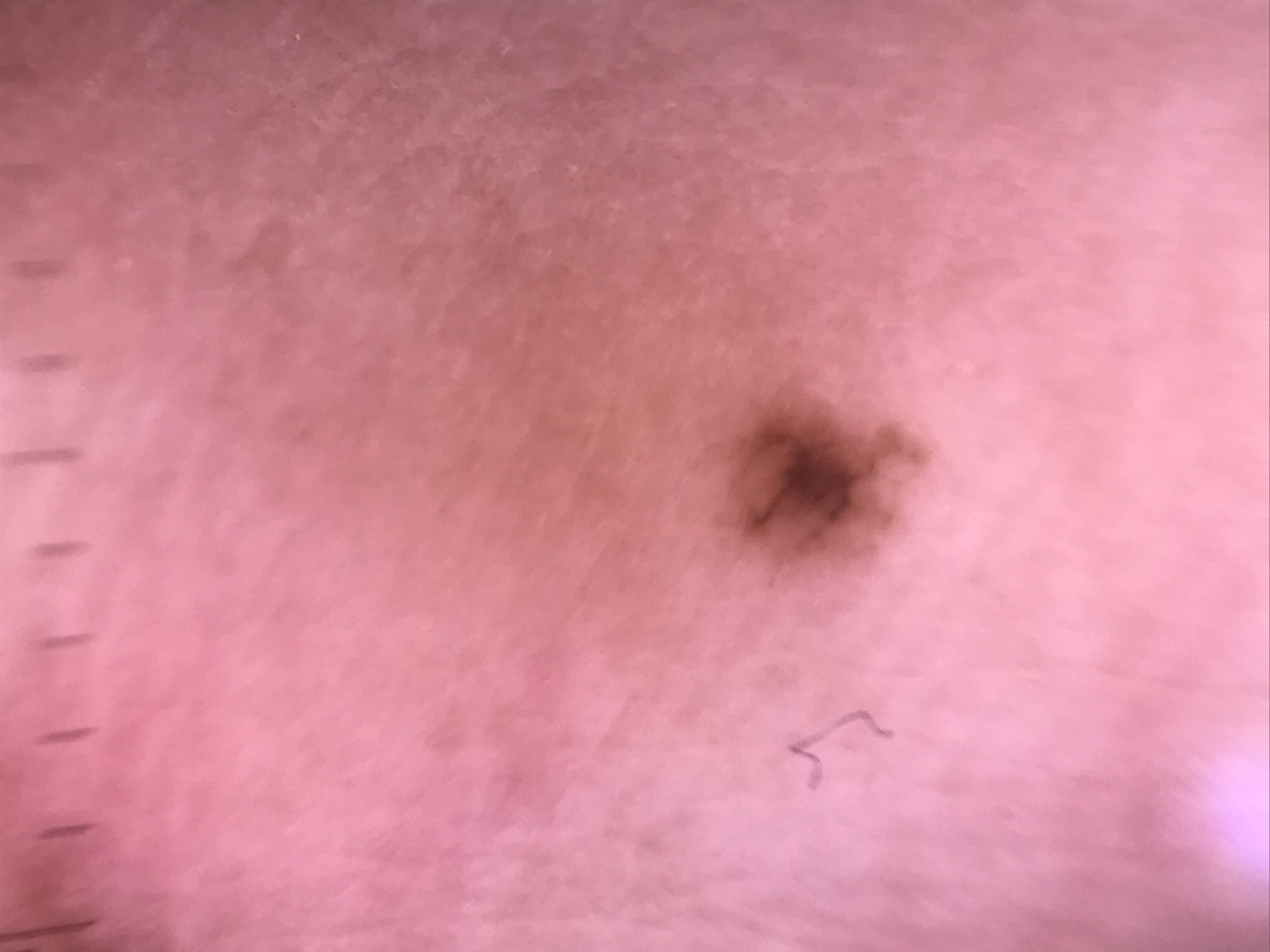A dermoscopy image of a single skin lesion. The diagnostic label was a banal lesion — an acral junctional nevus.